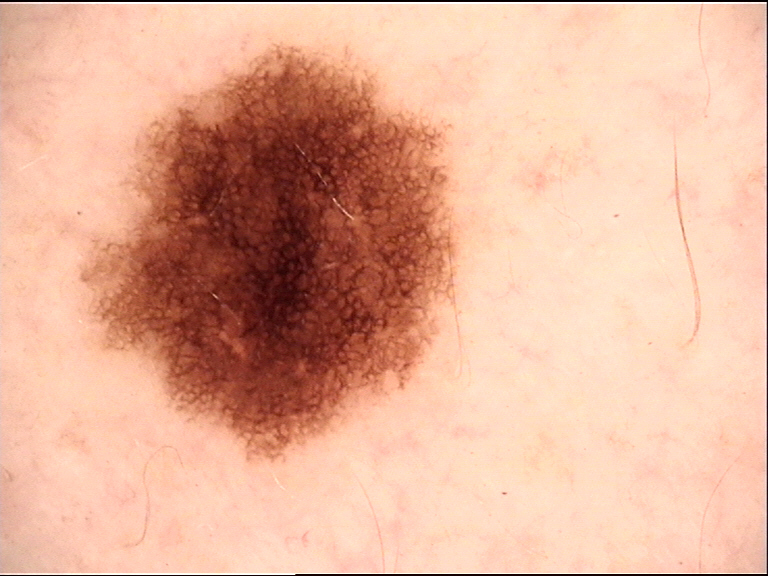Findings:
• image type: dermoscopy
• class: dysplastic junctional nevus (expert consensus)